A dermatoscopic image of a skin lesion:
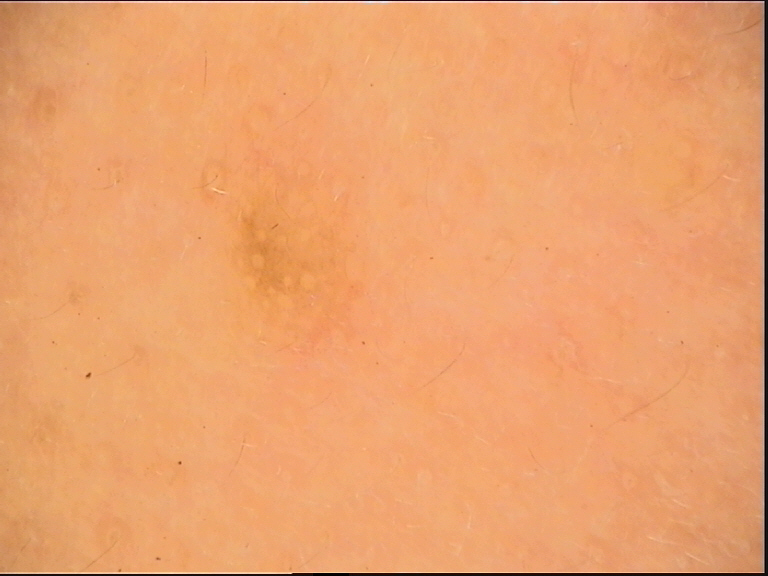Labeled as a Miescher nevus.